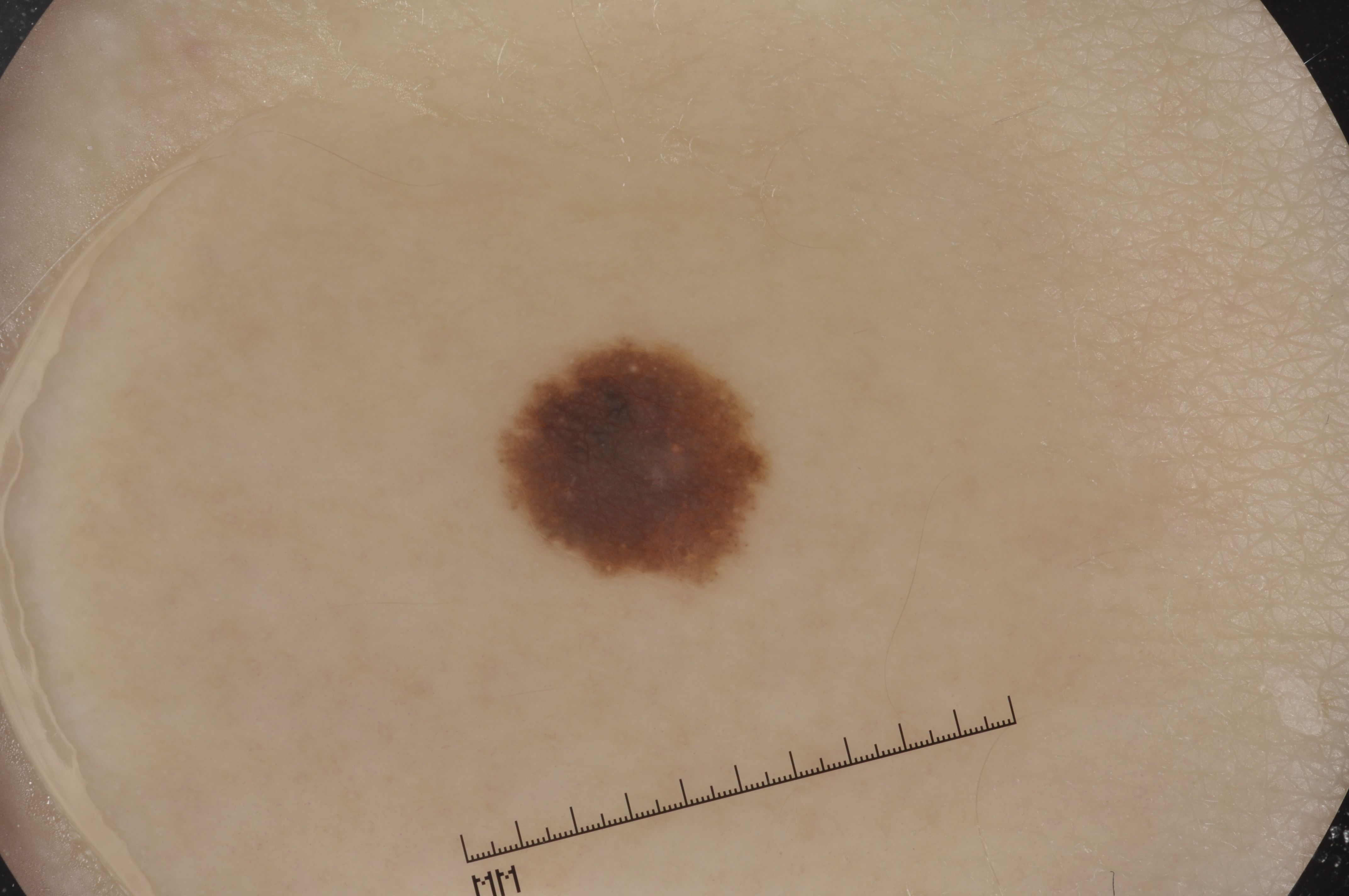A skin lesion imaged with a dermatoscope.
The lesion is bounded by [506,343,769,581].
Dermoscopic examination shows milia-like cysts; no pigment network, streaks, or negative network.
A small lesion occupying a minor part of the field.
Clinically diagnosed as a melanocytic nevus, a benign skin lesion.